Located on the head or neck, leg and arm · the photograph is a close-up of the affected area: 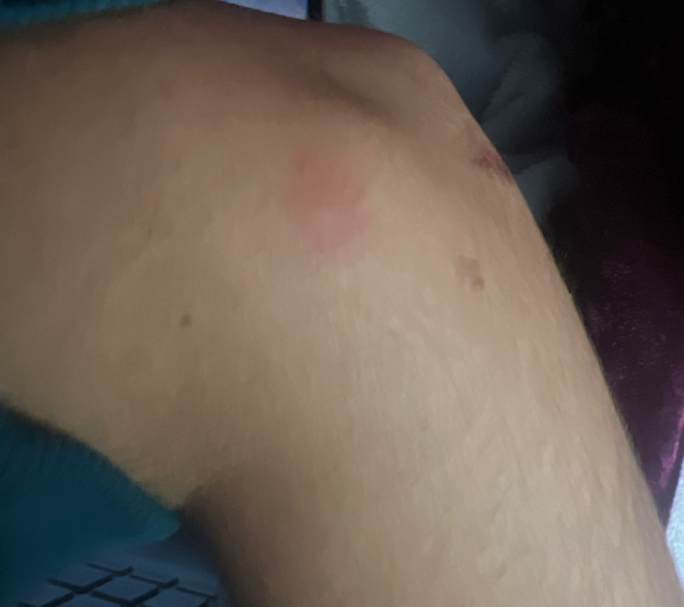No skin condition was discernible on photographic review.
The lesion is described as raised or bumpy.
The patient described the issue as a rash.
Symptoms reported: itching.
The contributor notes associated shortness of breath and fatigue.
Present for one to four weeks.